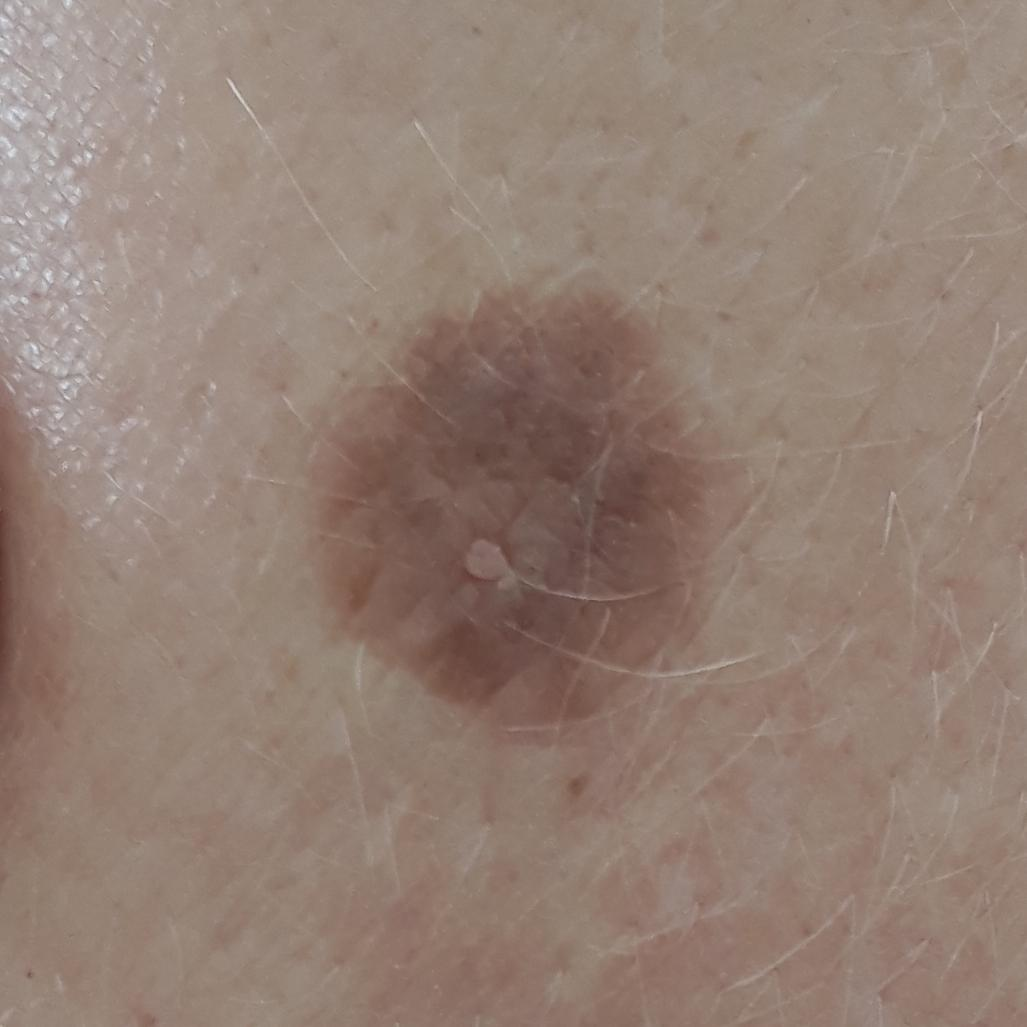Findings:
A subject in their 30s. A clinical photo of a skin lesion taken with a smartphone. Located on a forearm. The patient describes that the lesion is elevated and has grown.
Conclusion:
Diagnosed by dermatologist consensus as a nevus.